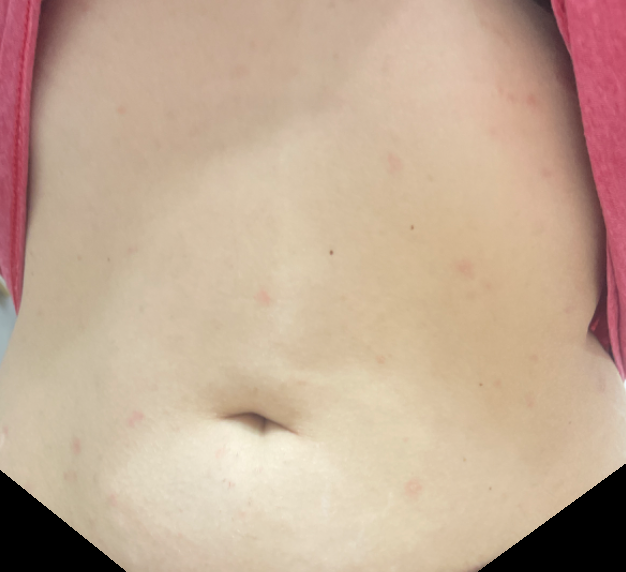Q: How was the photo taken?
A: at an angle
Q: Anatomic location?
A: front of the torso
Q: Reported symptoms?
A: bothersome appearance, burning, itching and enlargement
Q: What is the patient's skin tone?
A: Fitzpatrick skin type II; lay reviewers estimated 2 on the MST
Q: When did this start?
A: one to four weeks
Q: Patient's own categorization?
A: a rash
Q: How does the lesion feel?
A: rough or flaky
Q: Any systemic symptoms?
A: fatigue, shortness of breath, joint pain and chills
Q: What is the dermatologist's impression?
A: Pityriasis rosea (primary); Psoriasis (possible); Pityriasis lichenoides (remote)